This image was taken at a distance · female patient, age 30–39 · the affected area is the back of the hand: 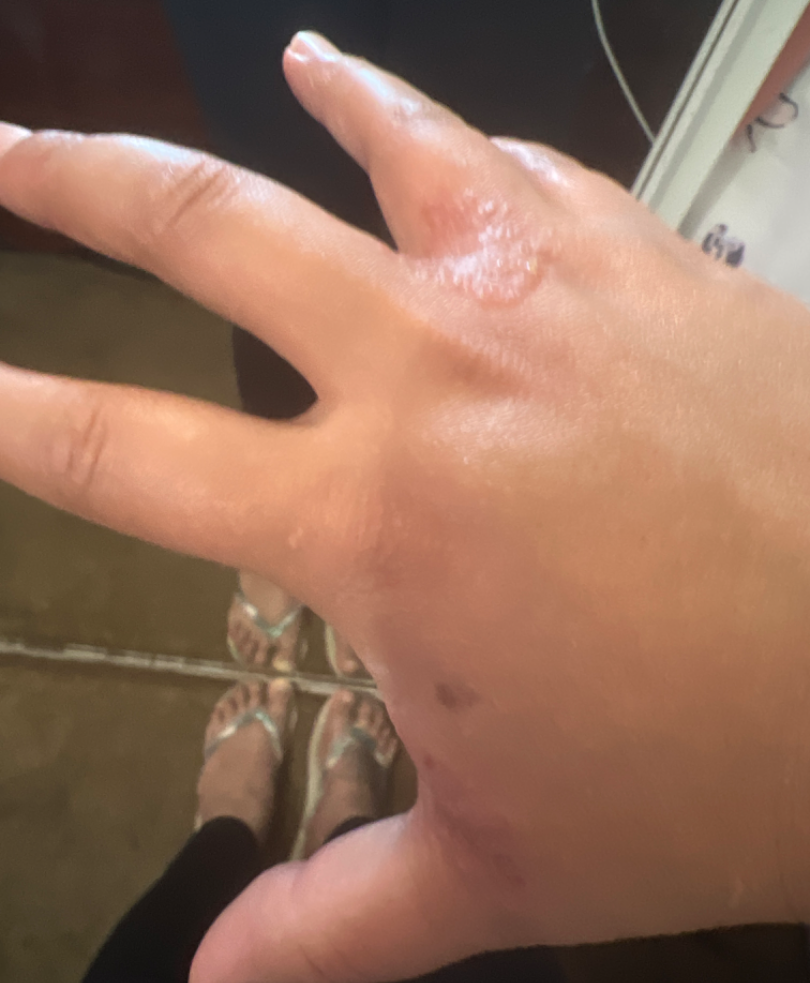On teledermatology review: Candida and Eczema were each considered, in no particular order; a remote consideration is Tinea; less probable is Psoriasis.